Dermoscopy of a skin lesion.
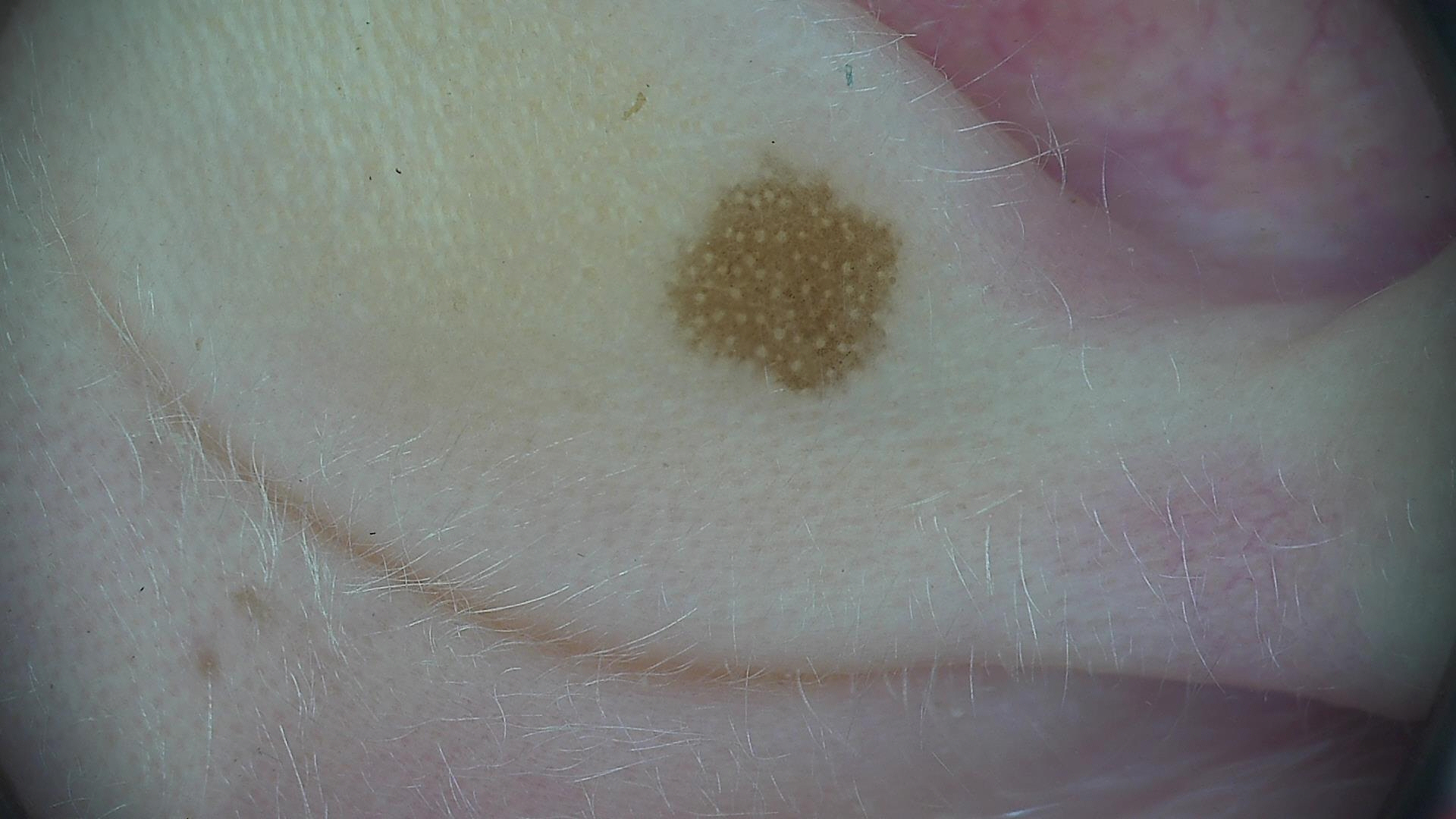assessment: dysplastic junctional nevus (expert consensus).